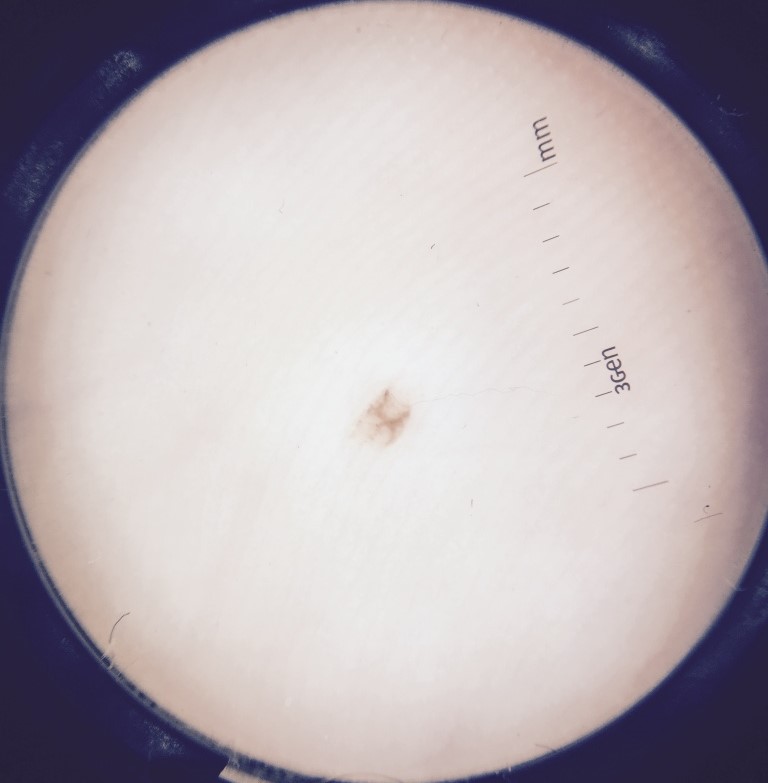Consistent with a benign lesion — an acral dysplastic junctional nevus.